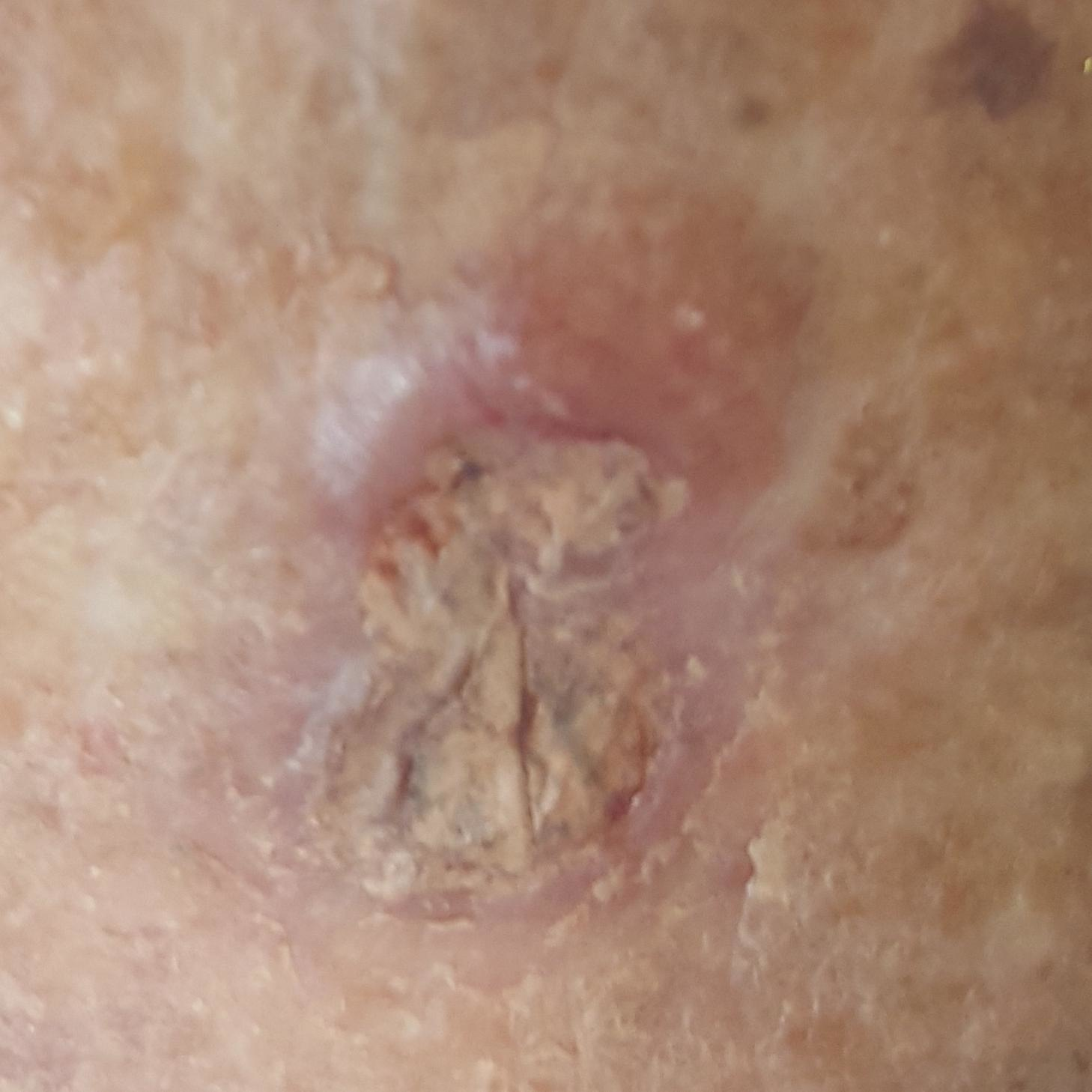Findings:
- FST — II
- risk factors — tobacco use, prior malignancy (patient or family), no alcohol use
- subject — female, in their 70s
- image type — smartphone clinical photo
- site — the nose
- lesion diameter — 6 × 4 mm
- symptoms — growth, itching, elevation / no pain, no bleeding
- pathology — basal cell carcinoma (biopsy-proven)